The patient is Fitzpatrick phototype I · the chart notes a previous melanoma · a male patient aged 73 to 77 — 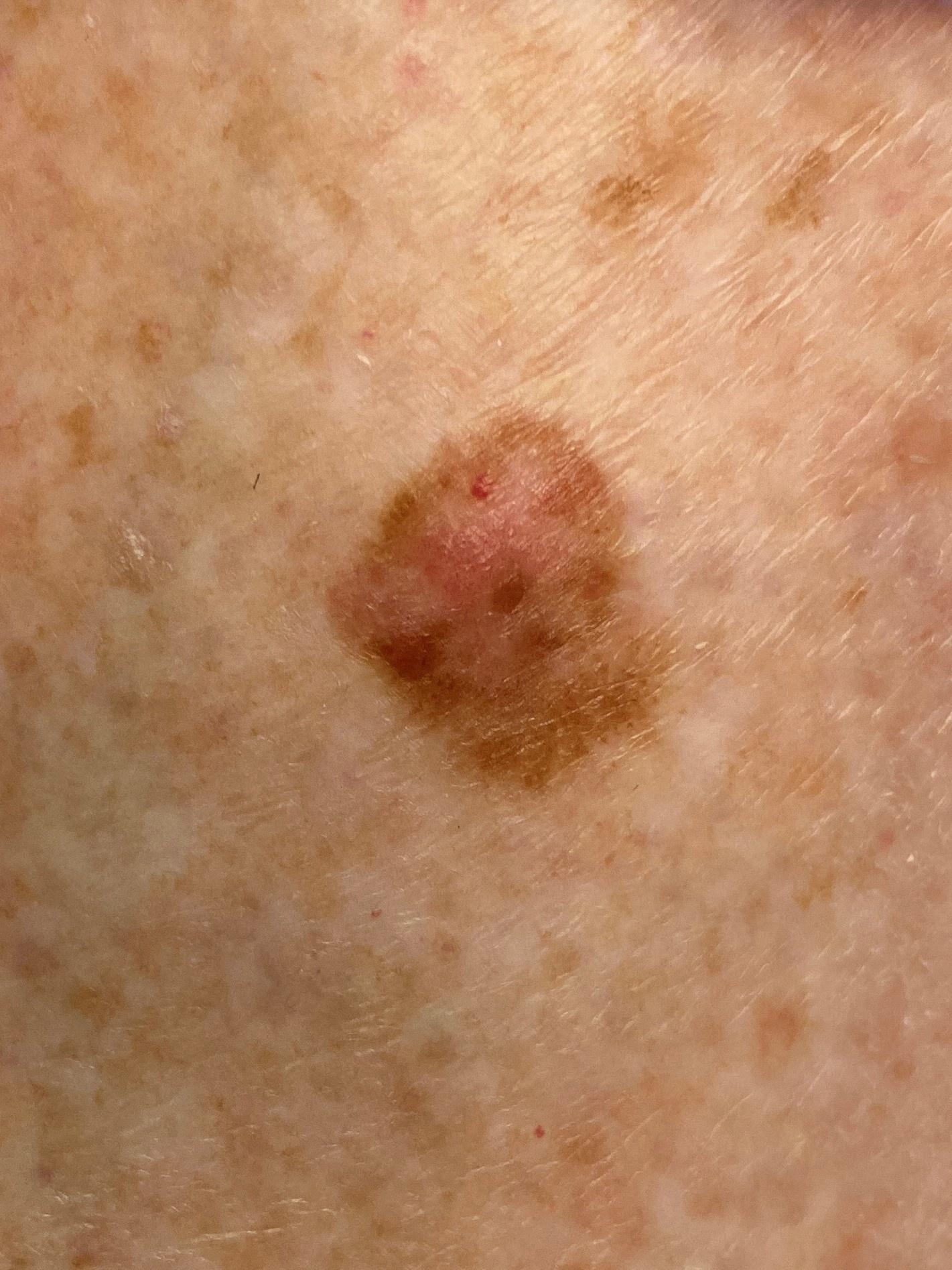The lesion involves a lower extremity. Histopathology confirmed a melanoma.